The subject is 30–39, female. Present for less than one week. Symptoms reported: itching, bothersome appearance and enlargement. An image taken at an angle. The patient considered this a rash. The patient reported no systemic symptoms. The lesion is described as raised or bumpy:
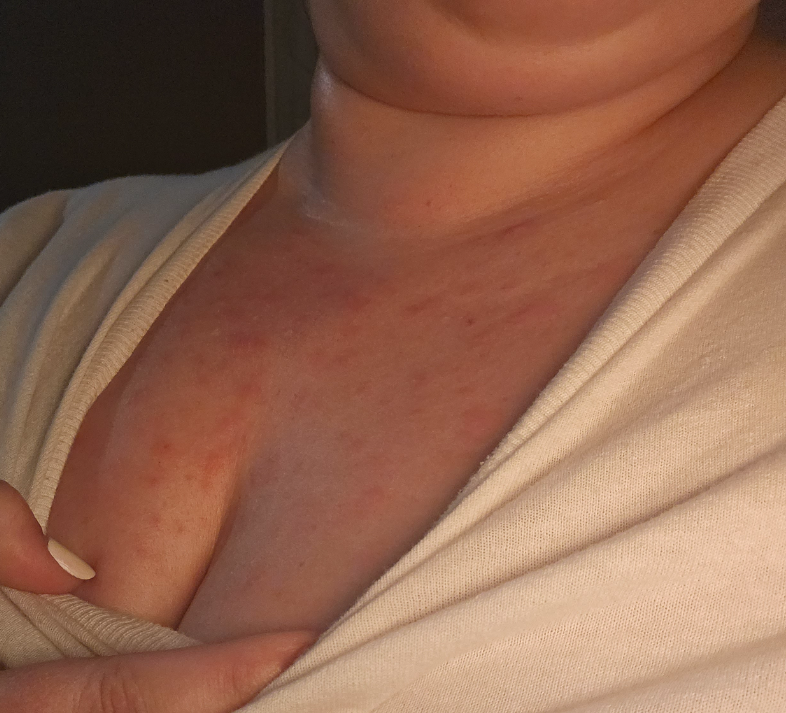The case was indeterminate on photographic review.